A female subject, aged around 35. A dermatoscopic image of a skin lesion:
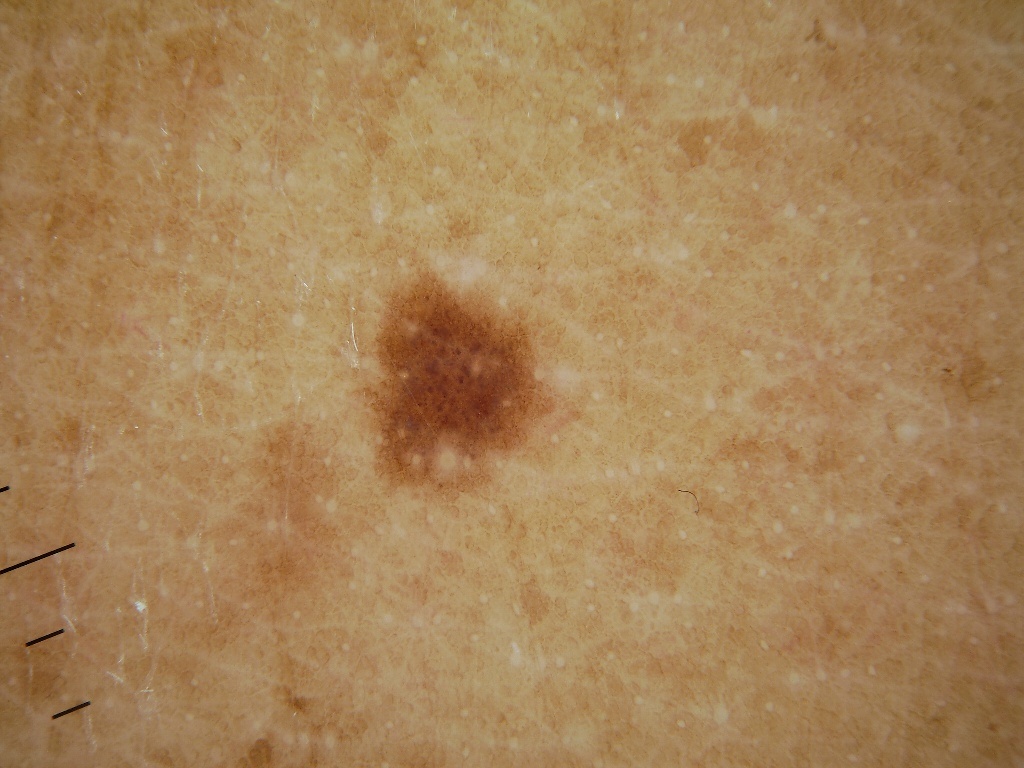Findings:
• lesion extent: ~4% of the field
• lesion bbox: 365, 274, 552, 496
• dermoscopic features: milia-like cysts and pigment network
• diagnostic label: a melanocytic nevus